The lesion involves the back of the torso, back of the hand and arm; this image was taken at an angle; the patient is 30–39, female: 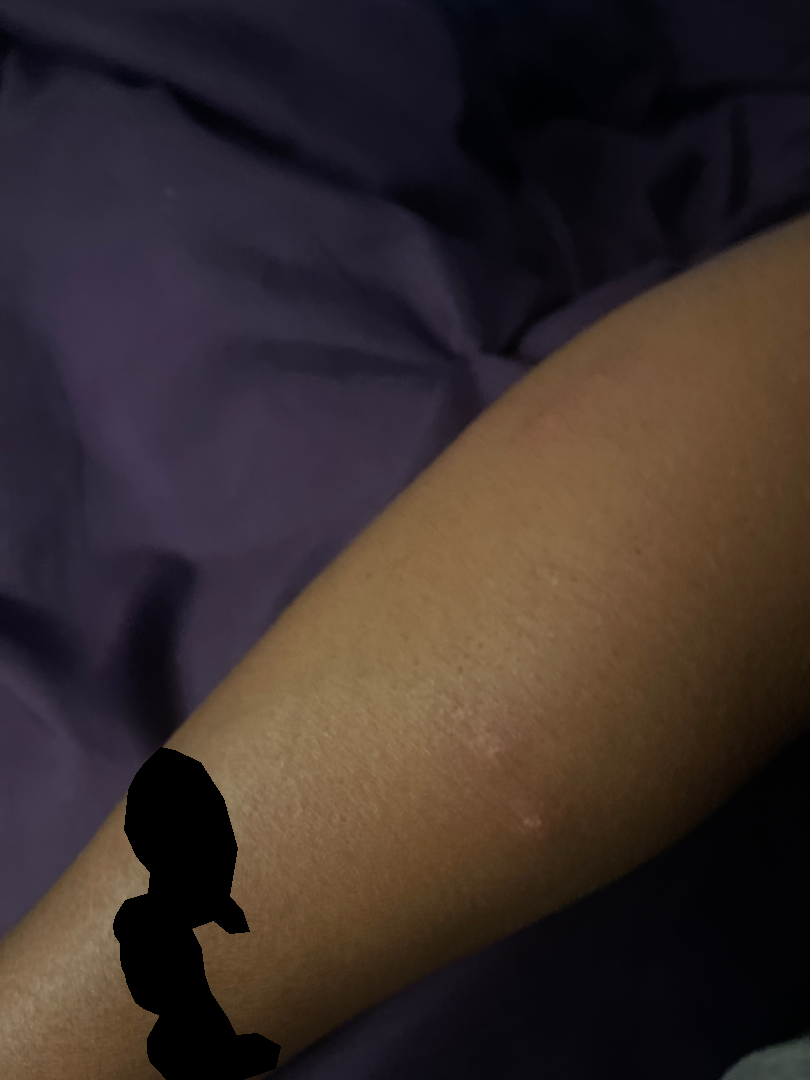The lesion is associated with itching. The patient indicates the lesion is raised or bumpy. Fitzpatrick phototype II. Reported duration is less than one week. The reviewer's impression was Insect Bite.